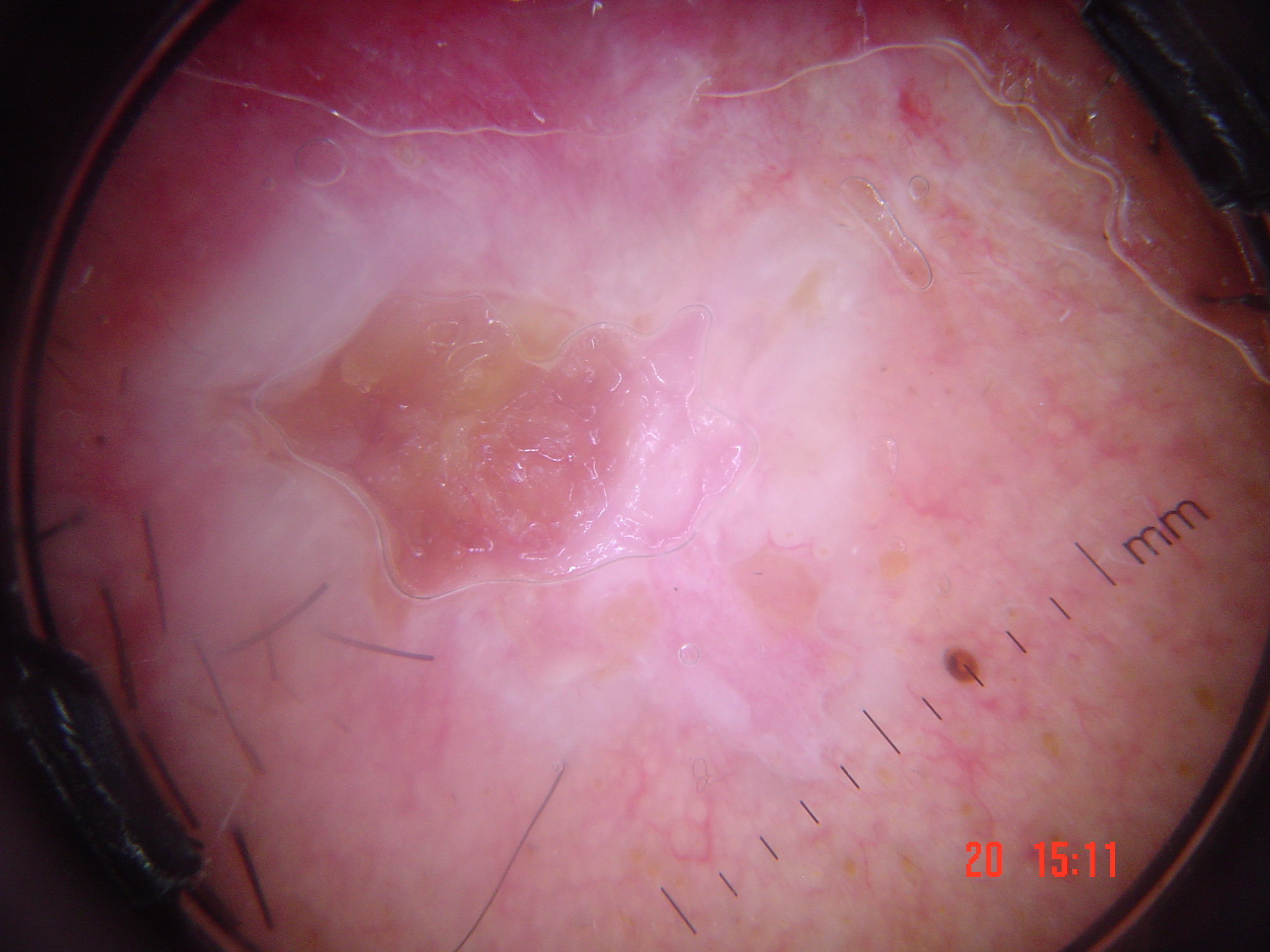imaging: dermatoscopy
lesion type: keratinocytic
diagnosis: squamous cell carcinoma (biopsy-proven)